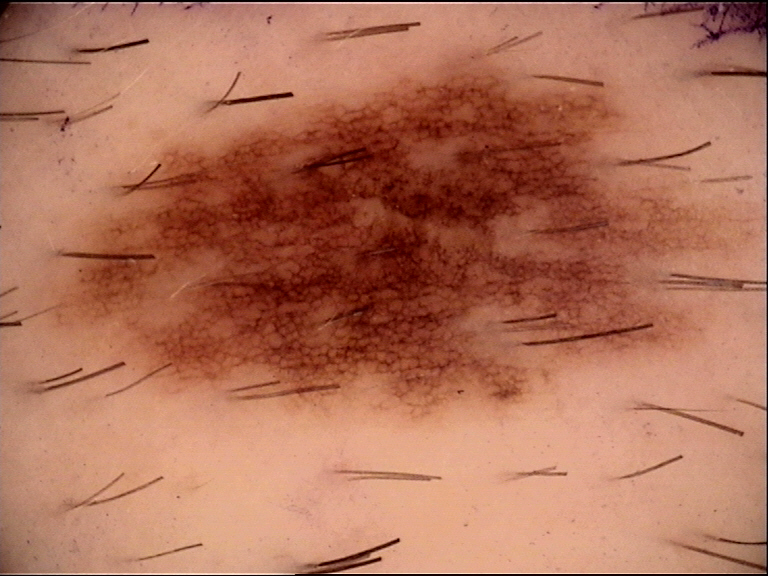imaging: dermatoscopy; assessment: dysplastic junctional nevus (expert consensus).